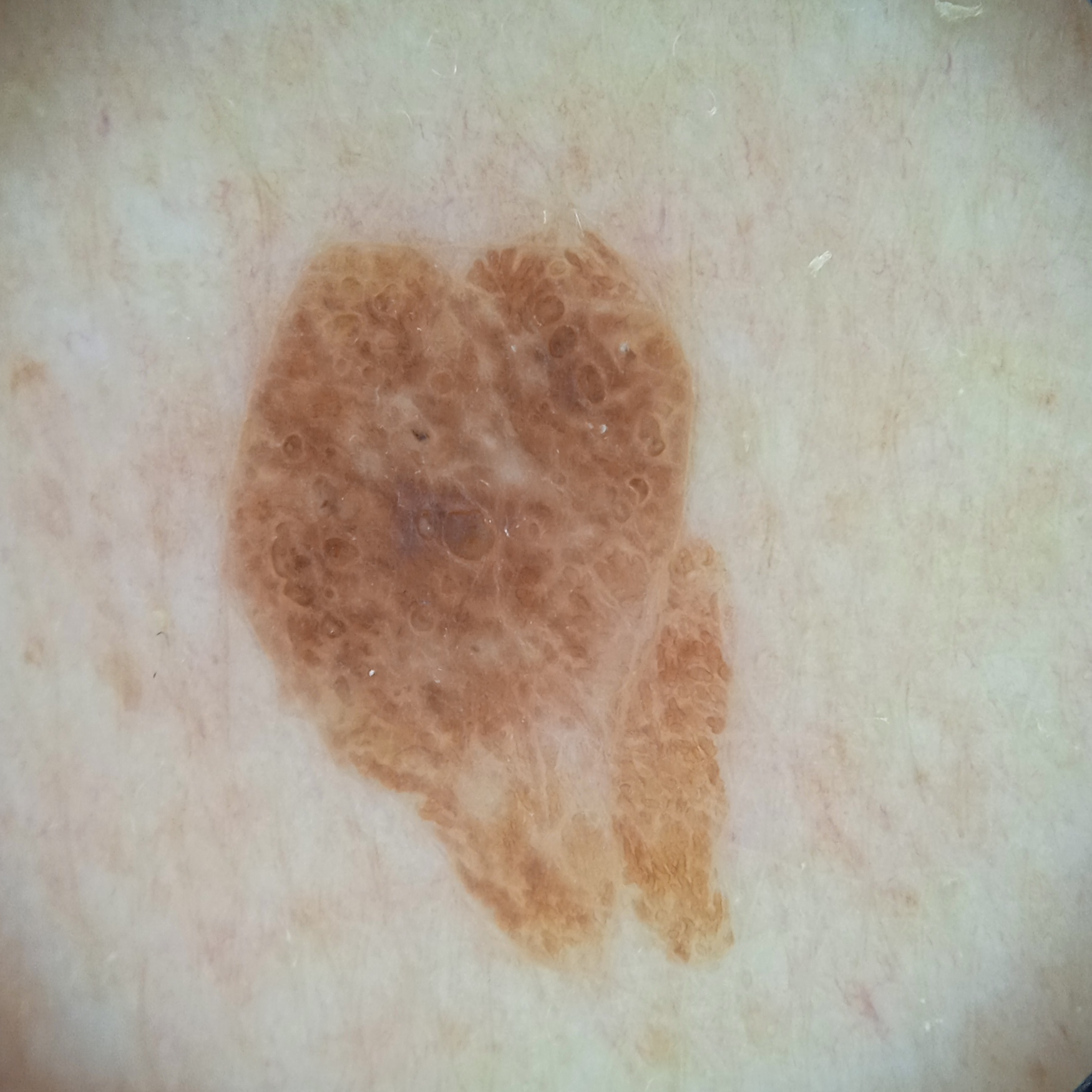Case summary:
Imaged for a research study, with no referral diagnosis recorded. A male subject 72 years old. A dermatoscopic image of a skin lesion. Located on the back. Measuring roughly 9.6 mm.
Assessment:
The four-dermatologist consensus diagnosis was a seborrheic keratosis.